Dermoscopy of a skin lesion:
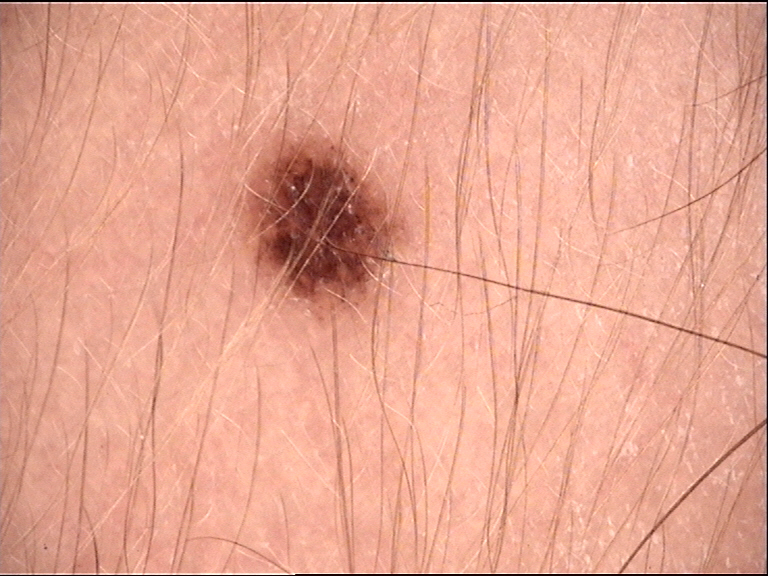The diagnosis was a dysplastic junctional nevus.